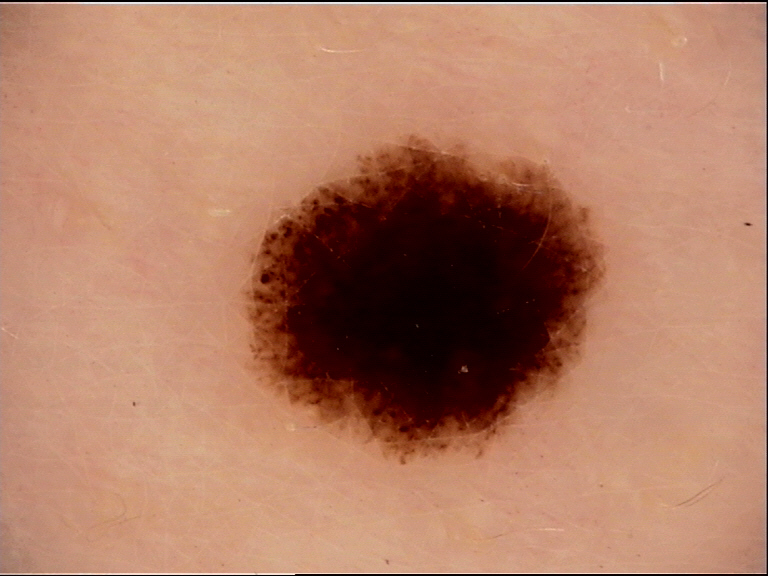Q: What is the lesion category?
A: banal
Q: What is the diagnosis?
A: compound nevus (expert consensus)